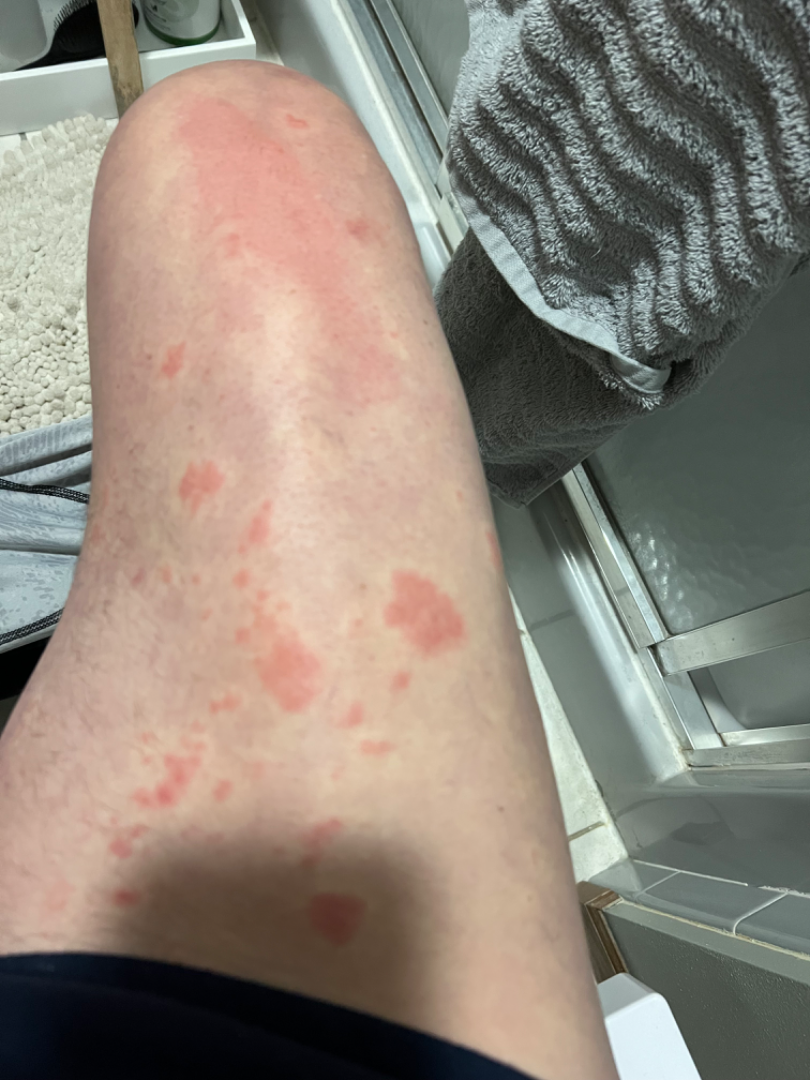Q: Image view?
A: close-up
Q: Anatomic location?
A: leg and back of the torso
Q: Patient demographics?
A: male, age 50–59
Q: What is the differential diagnosis?
A: most likely Urticaria; with consideration of Insect Bite; less likely is Allergic Contact Dermatitis